A dermoscopy image of a single skin lesion:
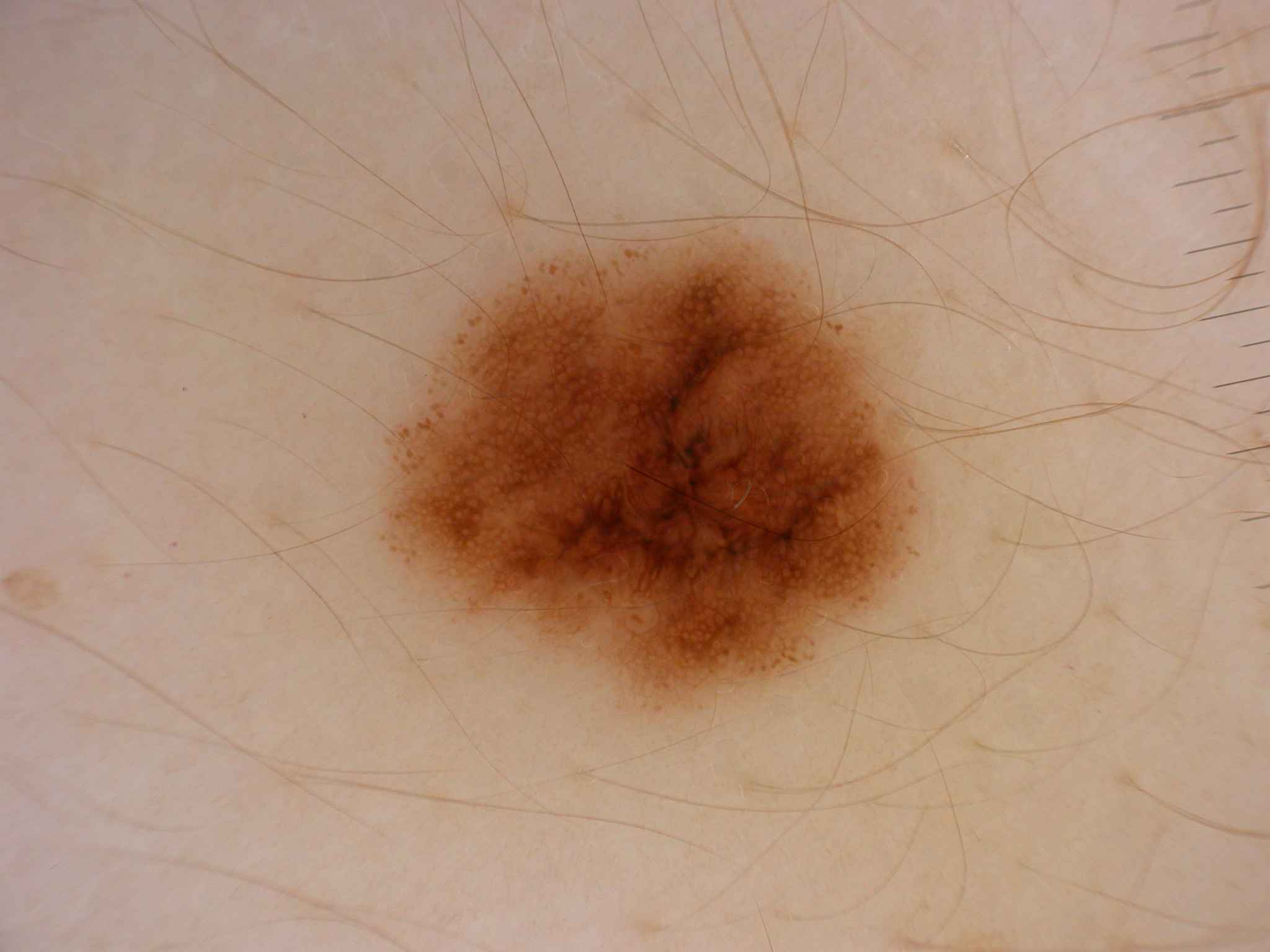Q: How much of the field does the lesion occupy?
A: ~15% of the field
Q: What dermoscopic features are present?
A: pigment network and globules
Q: Where is the lesion located?
A: 382/232/917/712
Q: What is the diagnosis?
A: a melanocytic nevus